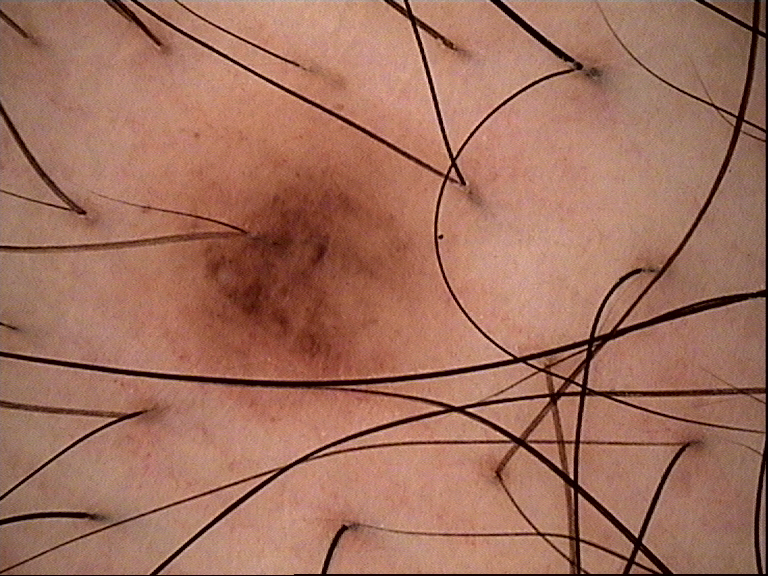Dermoscopy of a skin lesion.
The diagnostic label was a benign lesion — a dysplastic compound nevus.